The patient was assessed as FST II; a male patient 79 years of age; a clinical close-up photograph of a skin lesion; the chart records no prior malignancy (patient or family) and no tobacco use.
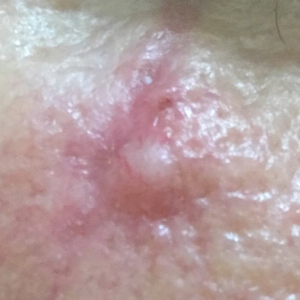location: the face | lesion size: approx. 10 × 8 mm | patient-reported symptoms: itching, elevation / no bleeding | diagnostic label: basal cell carcinoma (biopsy-proven).